A dermatoscopic image of a skin lesion.
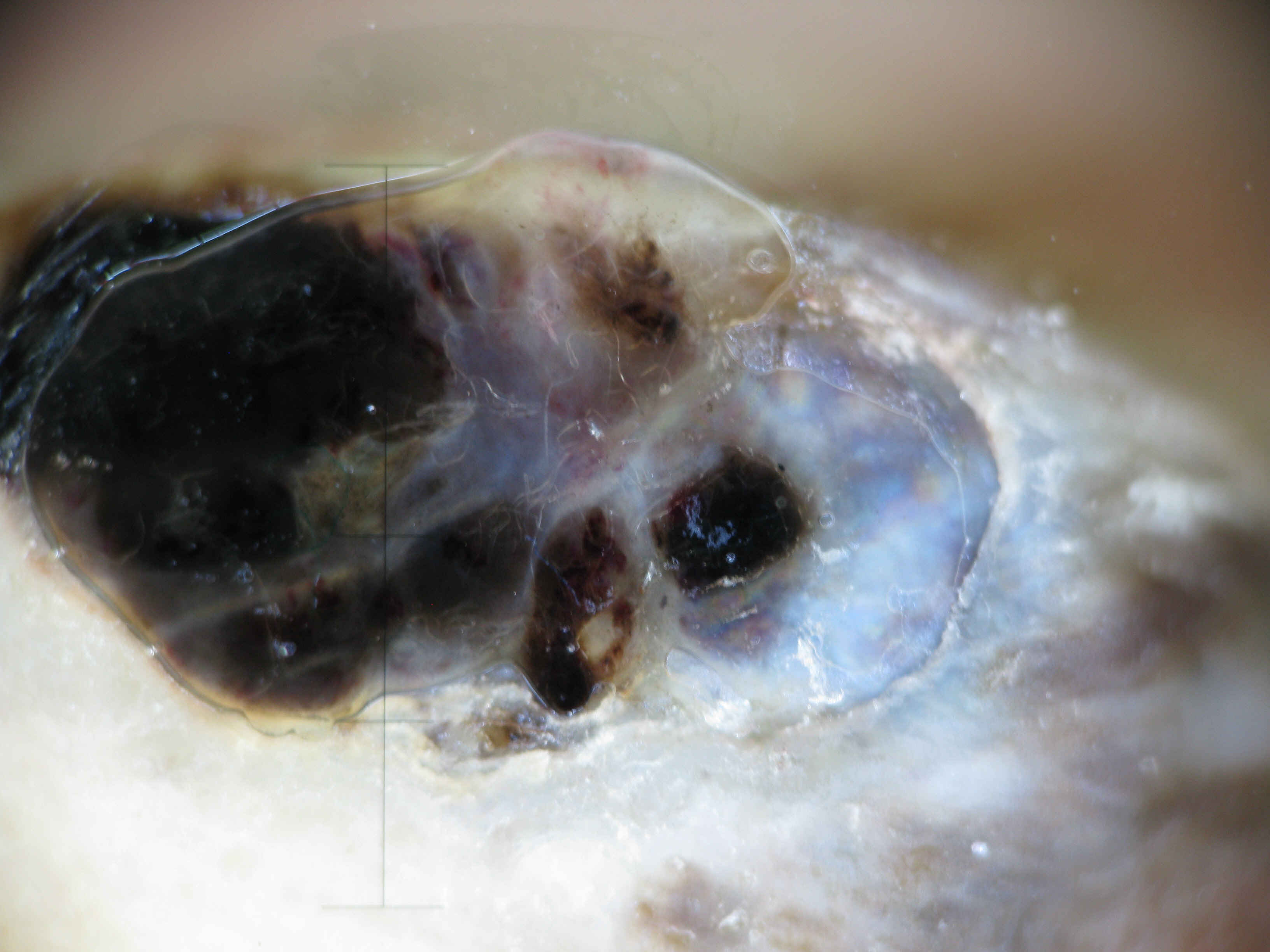Histopathologically confirmed as an acral nodular melanoma.